A clinical photograph showing a skin lesion. A subject age 62:
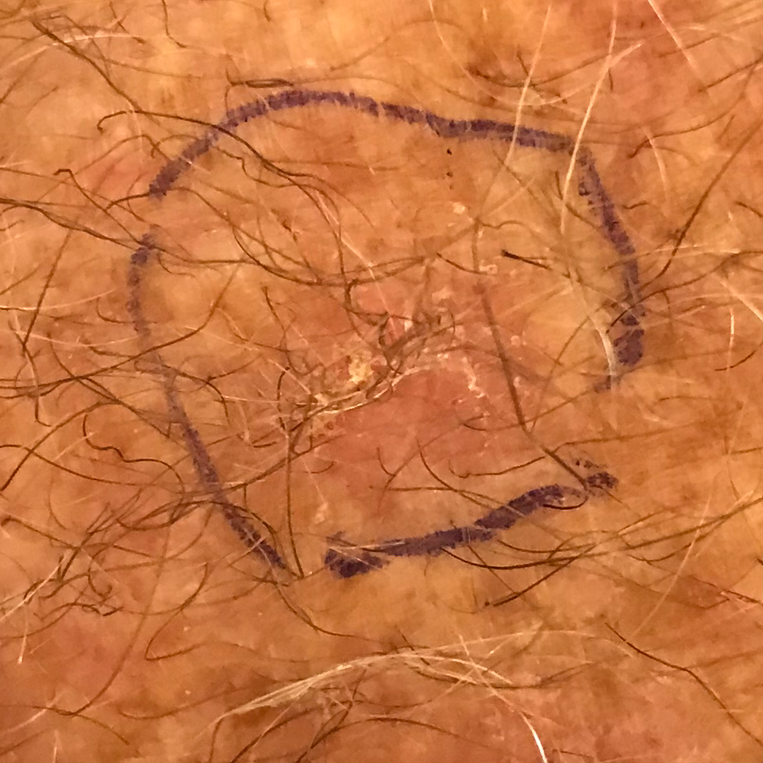Findings:
• anatomic site — an arm
• impression — actinic keratosis (clinical consensus)